A dermoscopy image of a single skin lesion: 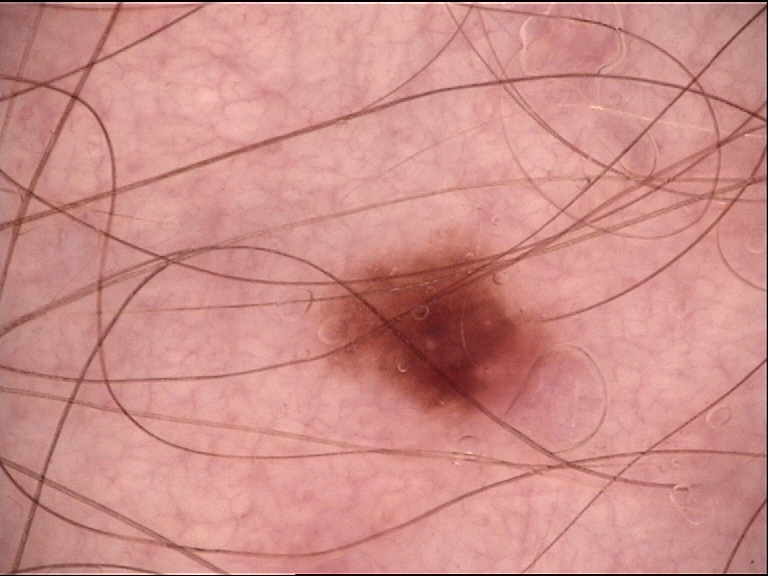Labeled as a dysplastic compound nevus.